The patient is skin type II; a male subject aged 78 to 82; an overview clinical photograph of a skin lesion — 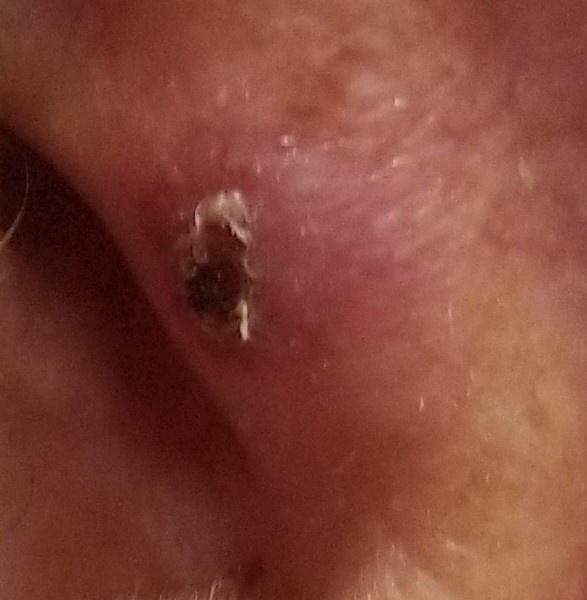The lesion is on the head or neck. Histopathological examination showed a squamous cell carcinoma.